A dermoscopic photograph of a skin lesion.
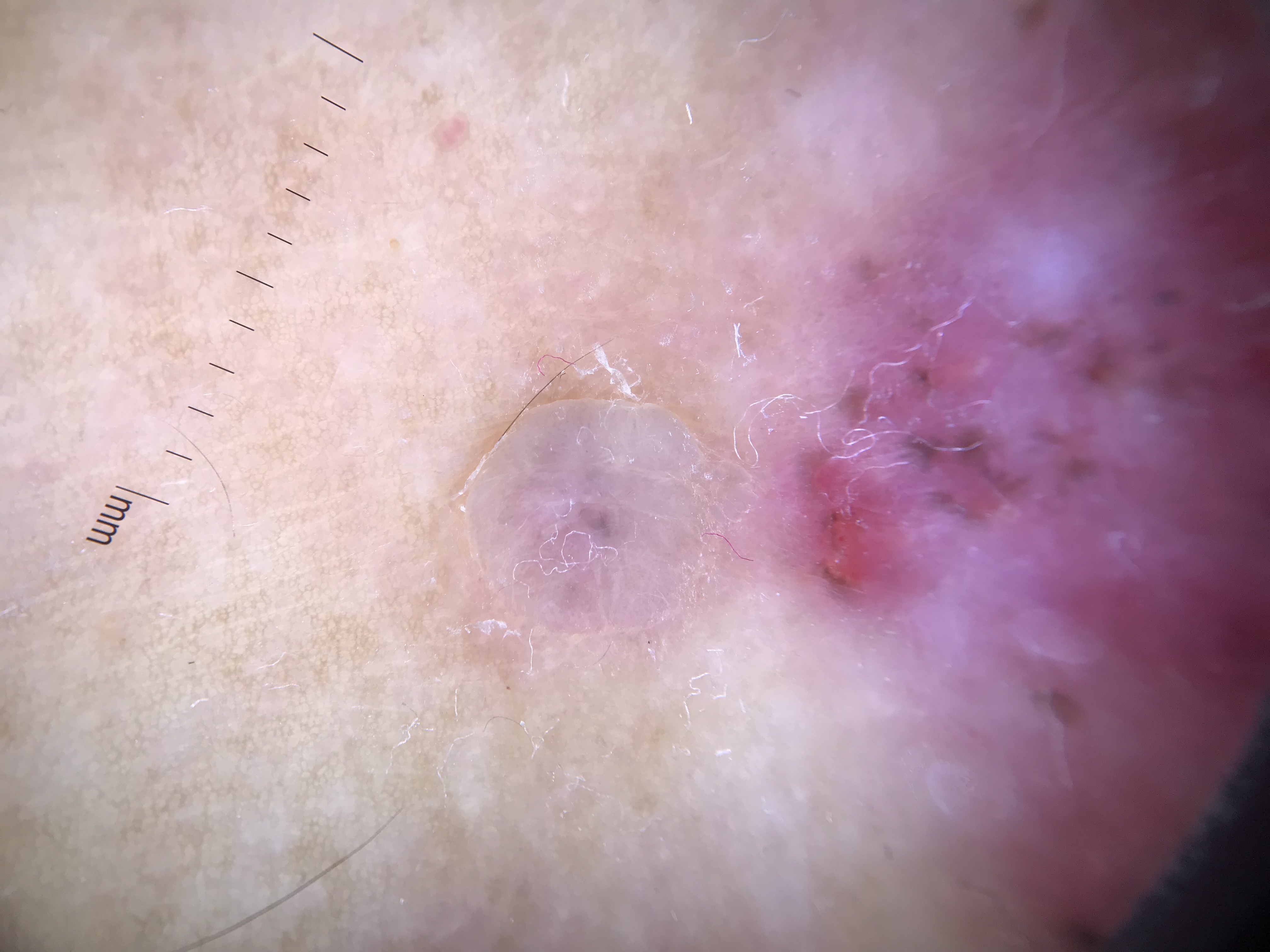Diagnosis:
Histopathology confirmed a keratinocytic, malignant lesion — a basal cell carcinoma.